No associated systemic symptoms reported. Self-categorized by the patient as skin that appeared healthy to them. The arm is involved. The lesion is described as fluid-filled. The patient indicates the condition has been present for one to four weeks. Close-up view. The lesion is associated with pain and burning — 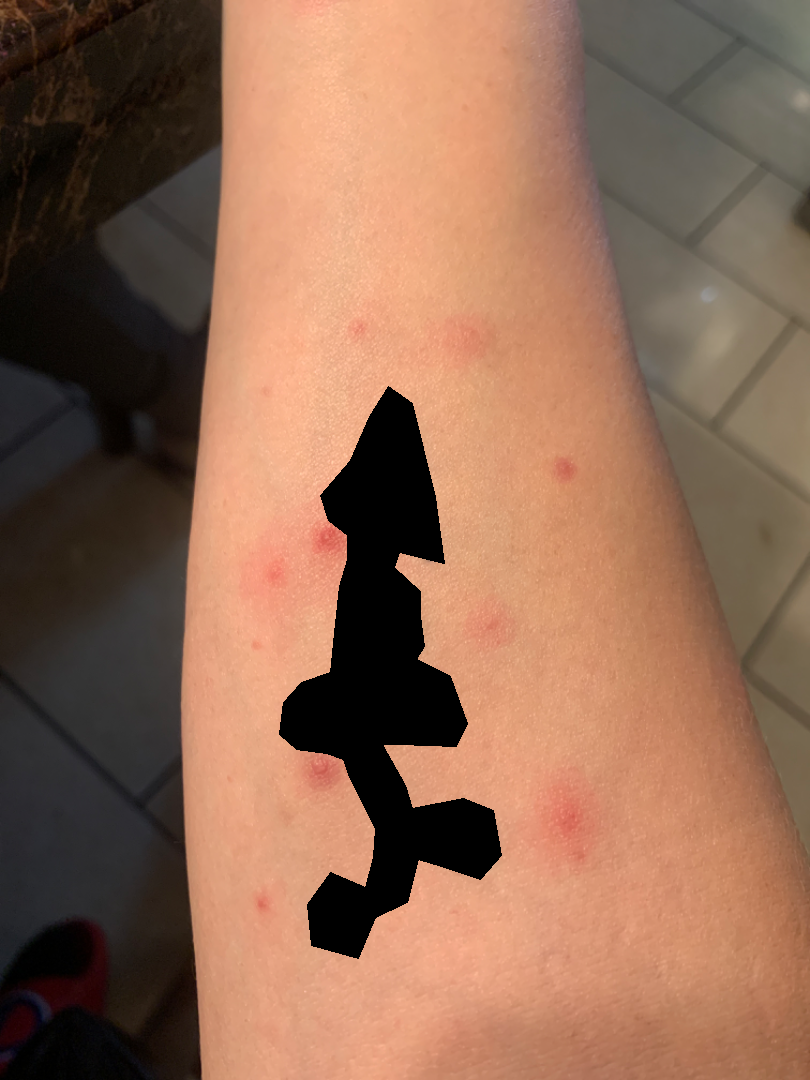On dermatologist assessment of the image, the primary impression is Insect Bite.